The photo was captured at a distance, the affected area is the arm:
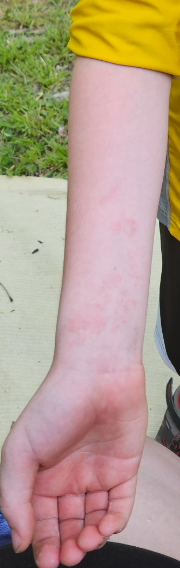On remote review of the image, Eczema (0.67); Allergic Contact Dermatitis (0.33).